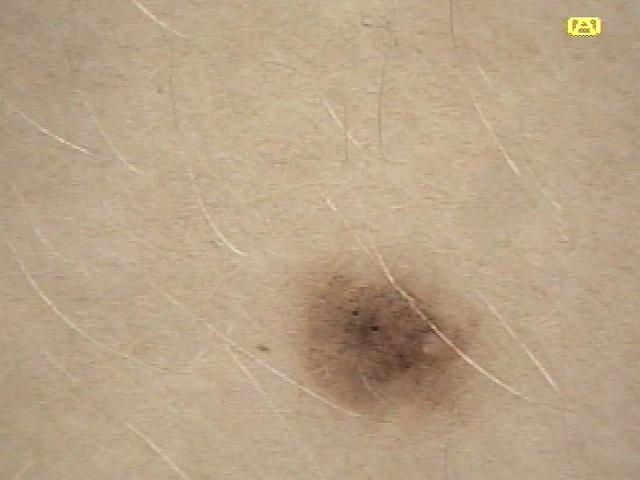Summary: A female patient roughly 20 years of age. Recorded as Fitzpatrick phototype II. A dermoscopic photograph of a skin lesion. Conclusion: Expert review favored a benign lesion — a nevus.